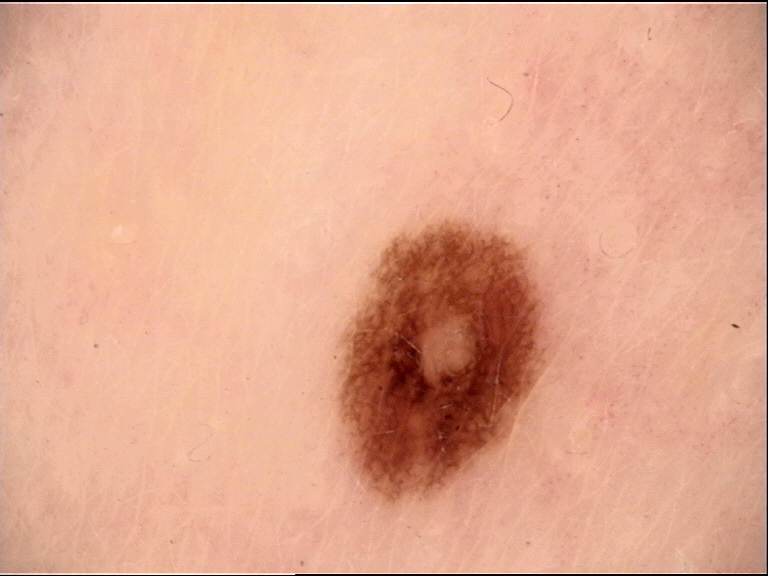image=dermoscopy | label=dysplastic junctional nevus (expert consensus).